A close-up photograph.
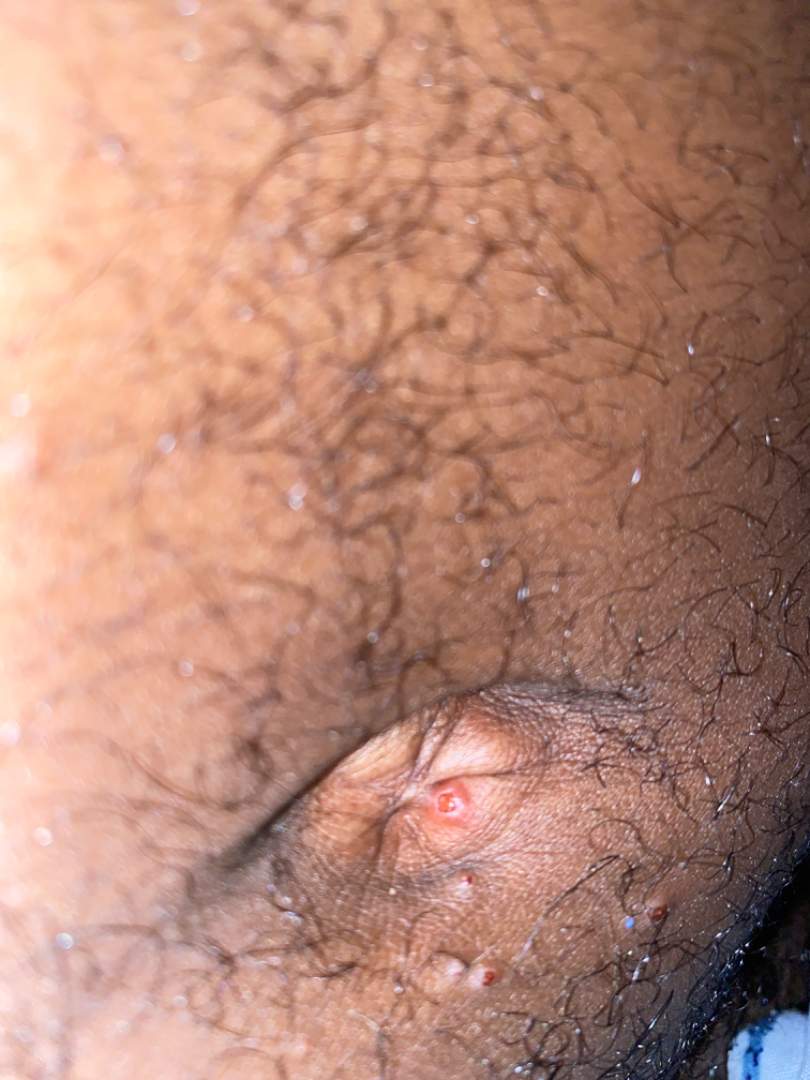History:
Skin tone: Fitzpatrick V.
Impression:
Skin infection (considered); Scabies (considered); Molluscum Contagiosum (considered).